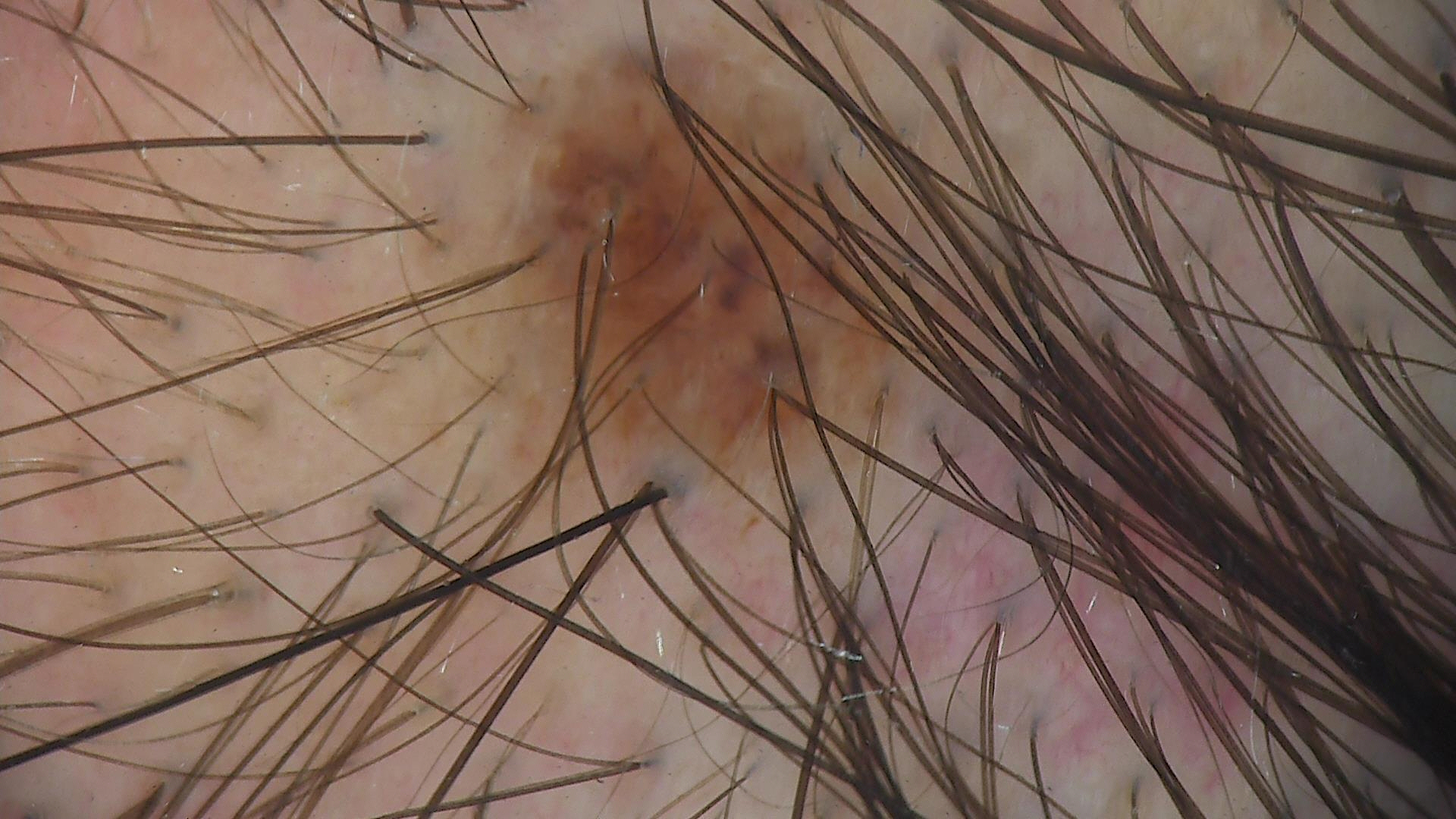Labeled as a dysplastic junctional nevus.